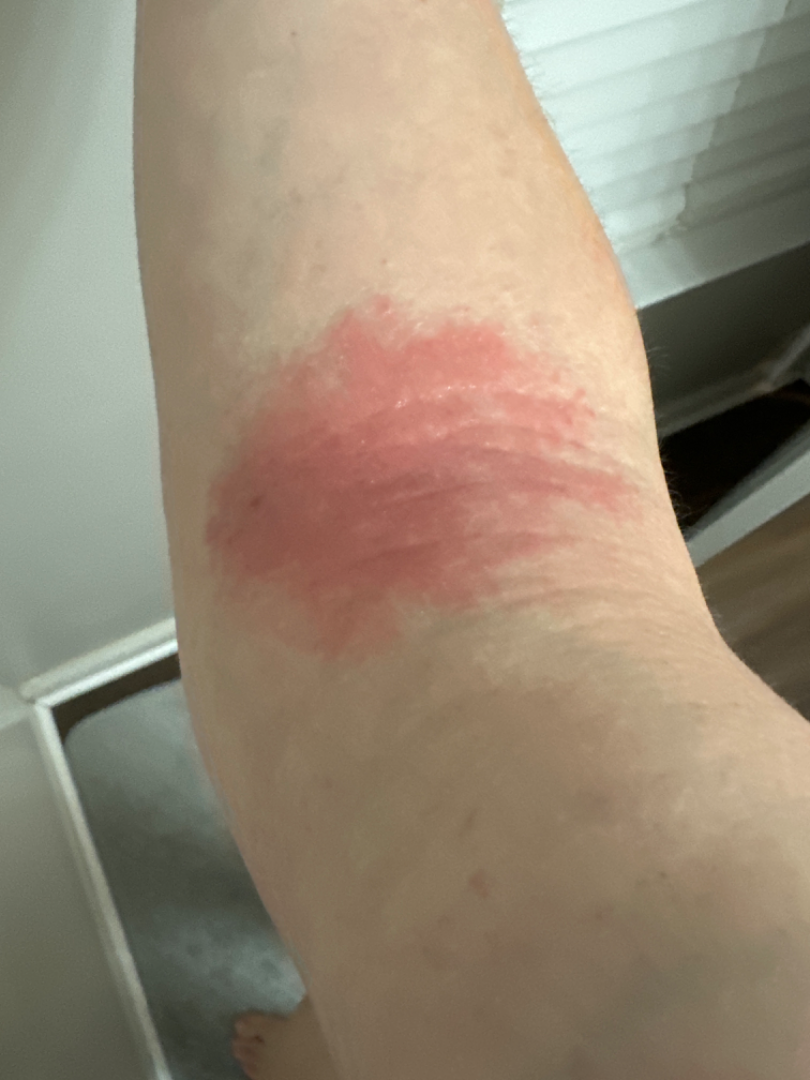A single dermatologist reviewed the case: Eczema and Allergic Contact Dermatitis were considered with similar weight; lower on the differential is Psoriasis.